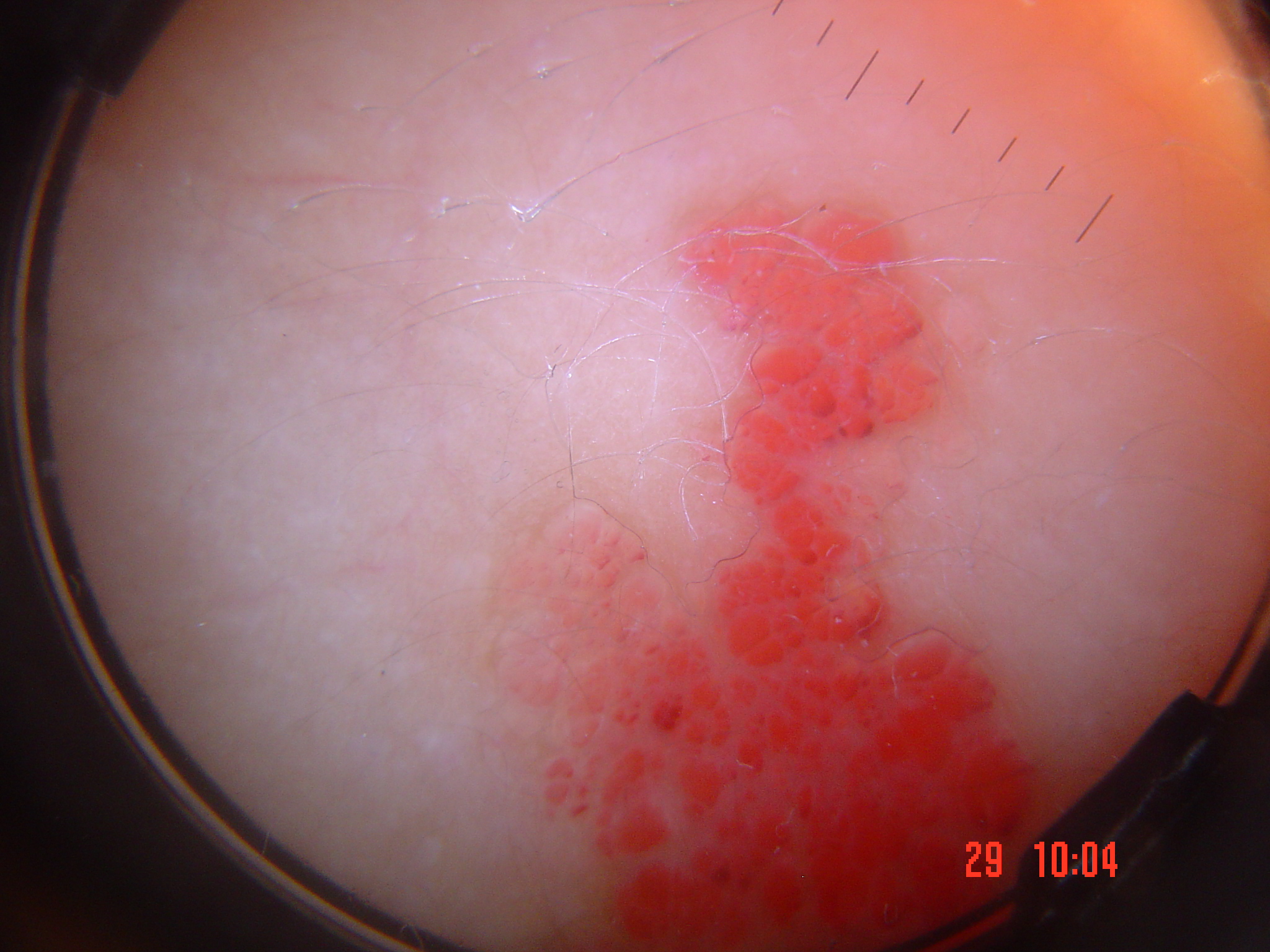Summary:
A dermoscopic photograph of a skin lesion.
Conclusion:
The diagnostic label was a vascular lesion — a lymphangioma.